A dermoscopy image of a single skin lesion.
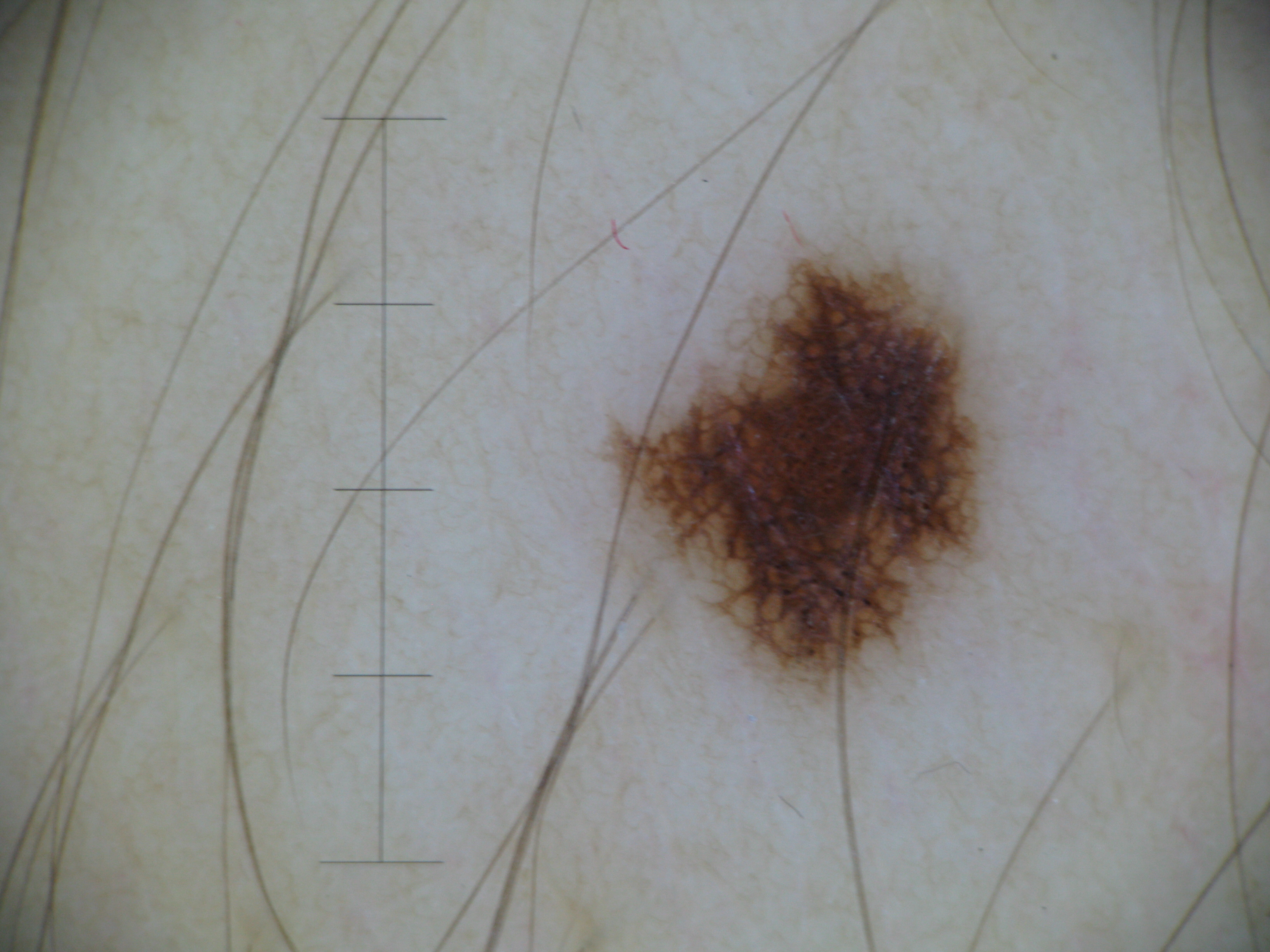classification = banal; label = junctional nevus (expert consensus).